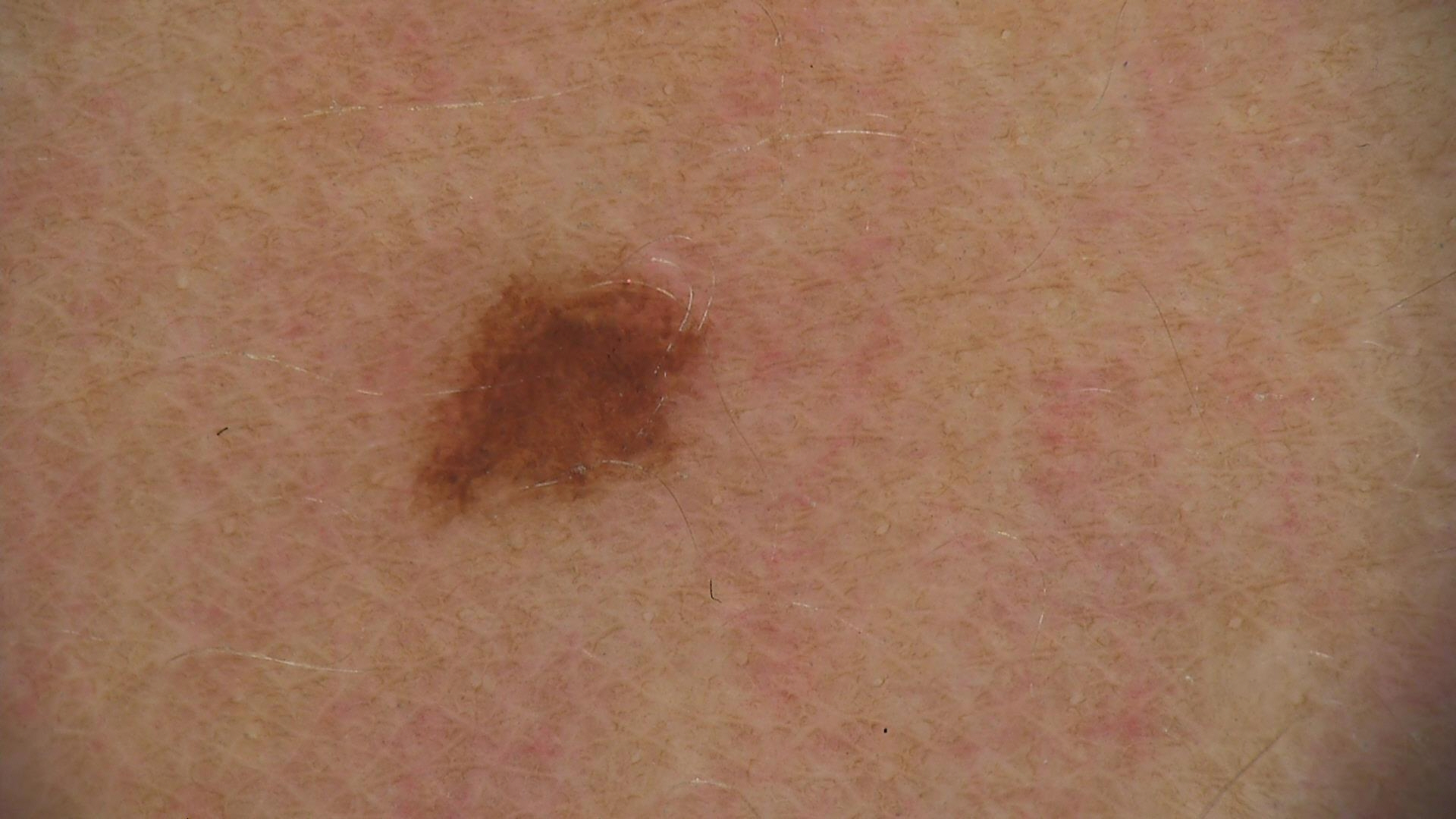<lesion>
<image>dermoscopy</image>
<diagnosis>
<name>dysplastic junctional nevus</name>
<code>jd</code>
<malignancy>benign</malignancy>
<super_class>melanocytic</super_class>
<confirmation>expert consensus</confirmation>
</diagnosis>
</lesion>